A female subject approximately 85 years of age or older · the patient is Fitzpatrick skin type II.
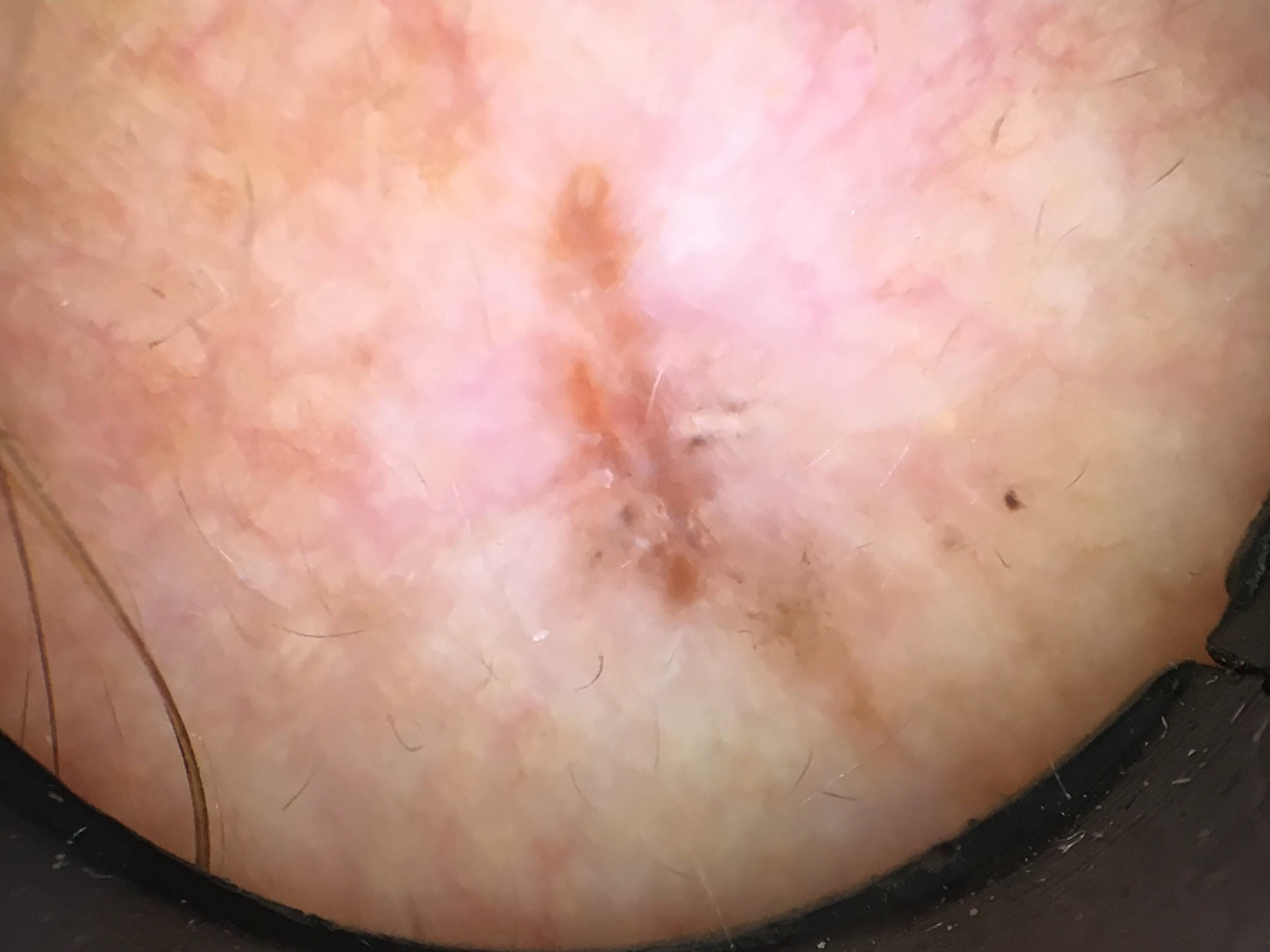{
  "lesion_location": {
    "region": "the head or neck"
  },
  "diagnosis": {
    "name": "Basal cell carcinoma",
    "malignancy": "malignant",
    "confirmation": "histopathology",
    "lineage": "adnexal"
  }
}